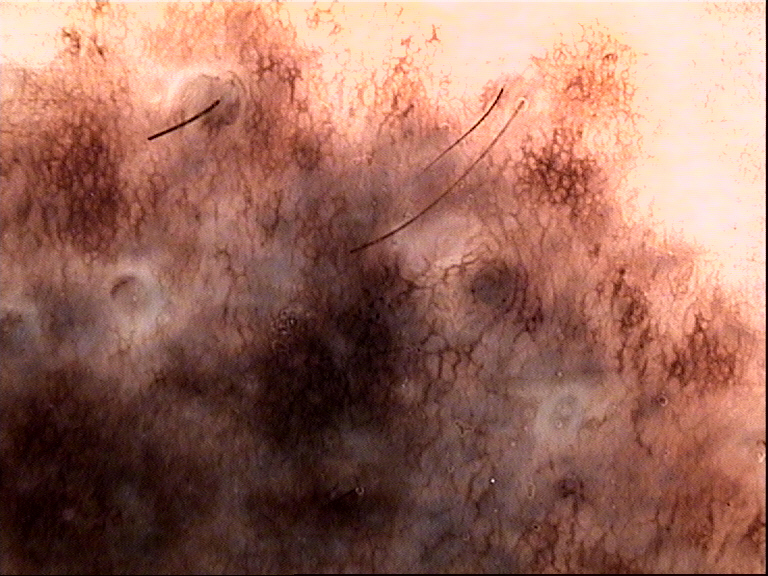Dermoscopy of a skin lesion. The morphology is that of a banal lesion. The diagnostic label was a congenital compound nevus.